A dermoscopic photograph of a skin lesion.
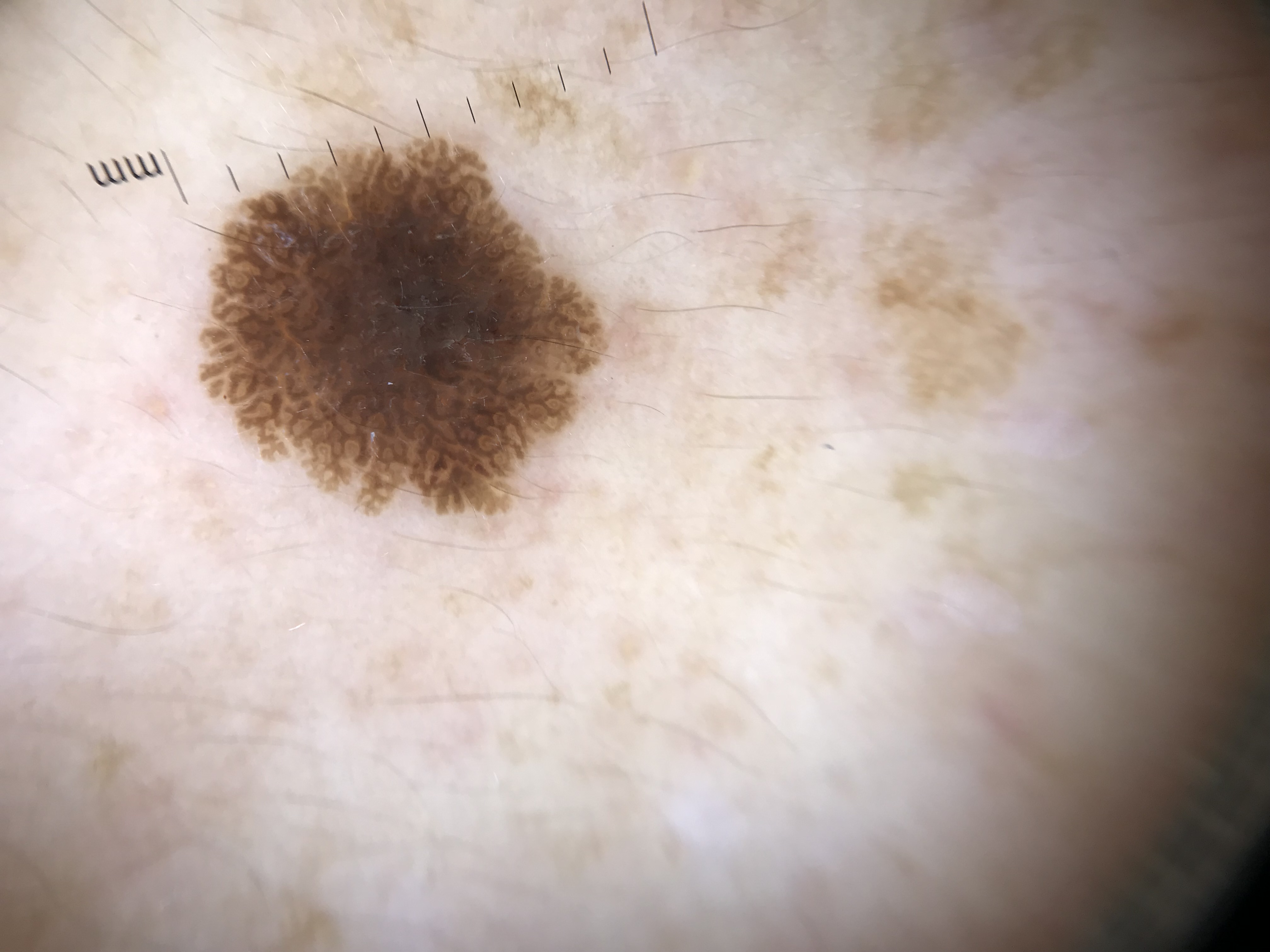diagnostic label — seborrheic keratosis (expert consensus).